The patient was assessed as FST II; a skin lesion imaged with contact-polarized dermoscopy; a male patient about 70 years old — 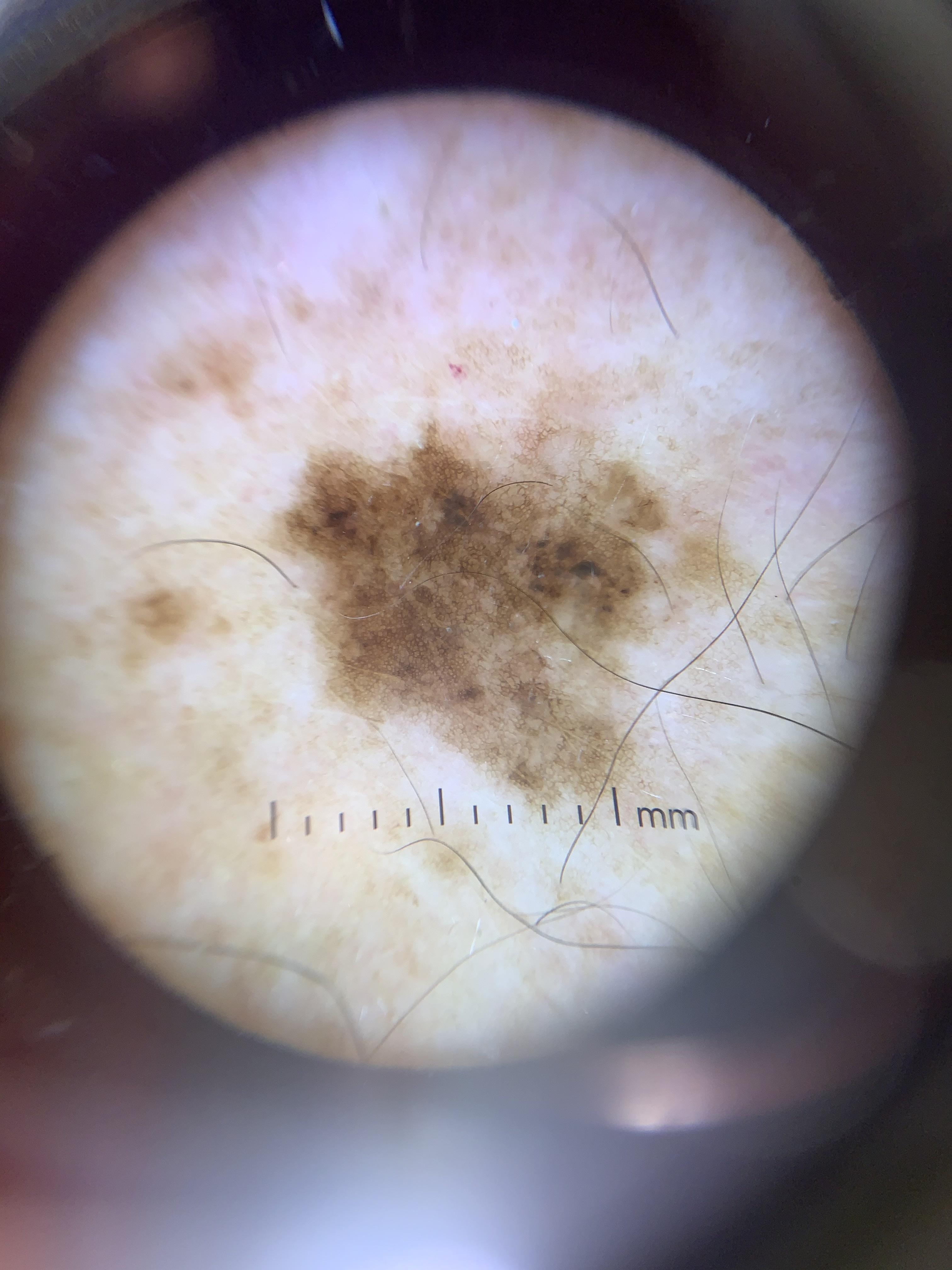Case:
• location — the trunk (the posterior trunk)
• diagnostic label — Nevus (biopsy-proven)